A dermoscopy image of a single skin lesion.
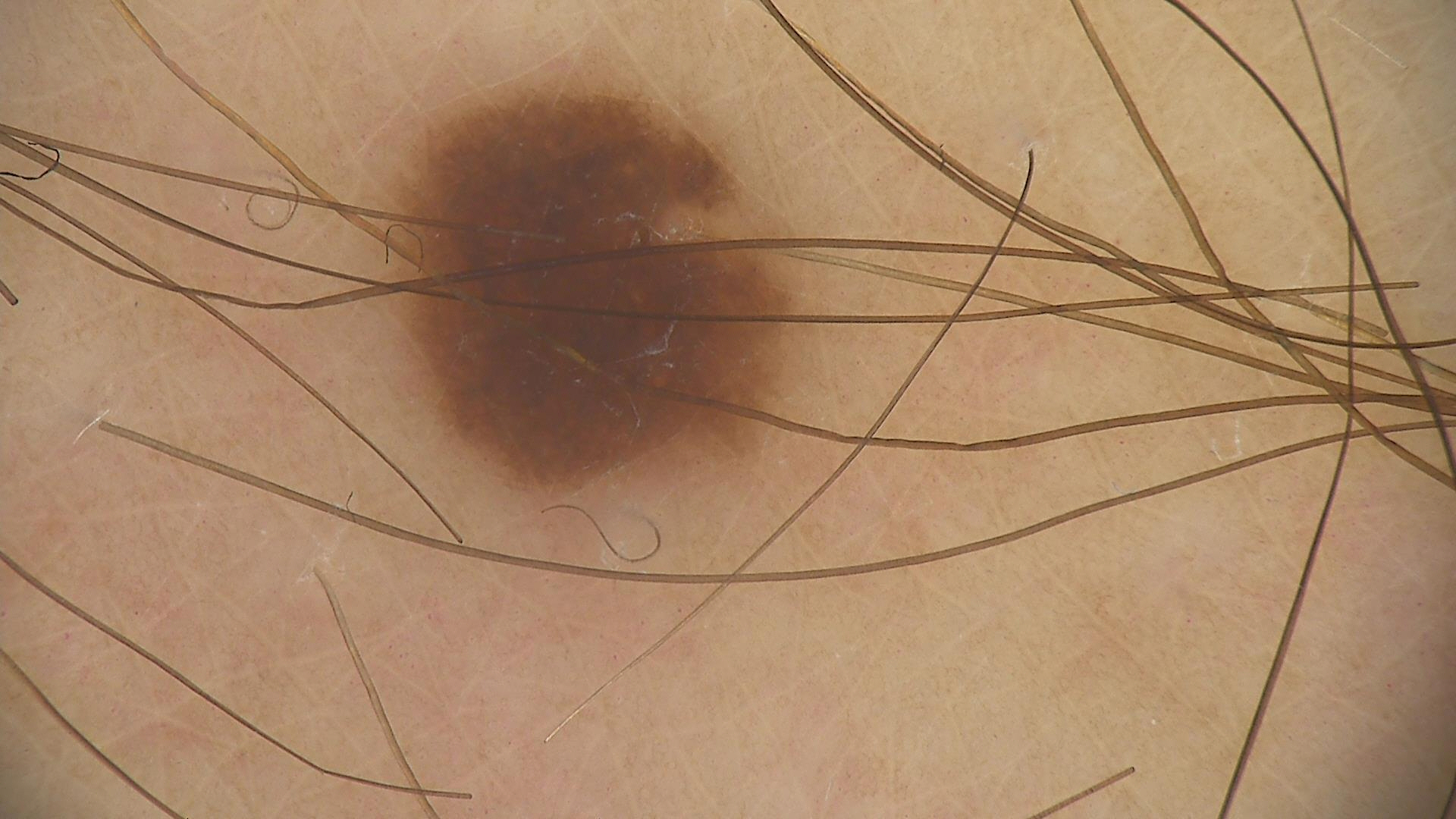Labeled as a dysplastic junctional nevus.